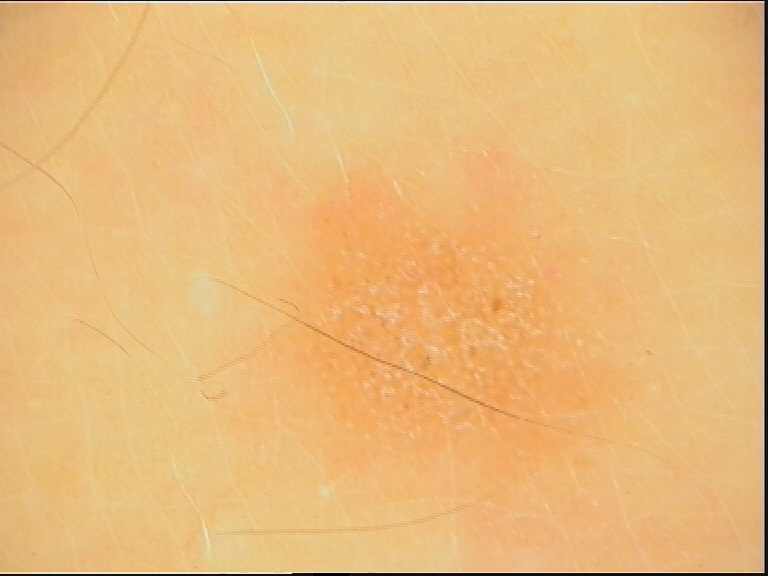A dermoscopic photograph of a skin lesion.
The diagnostic label was a keratinocytic lesion — a seborrheic keratosis.